The photograph was taken at an angle. The head or neck is involved. Reported duration is less than one week — 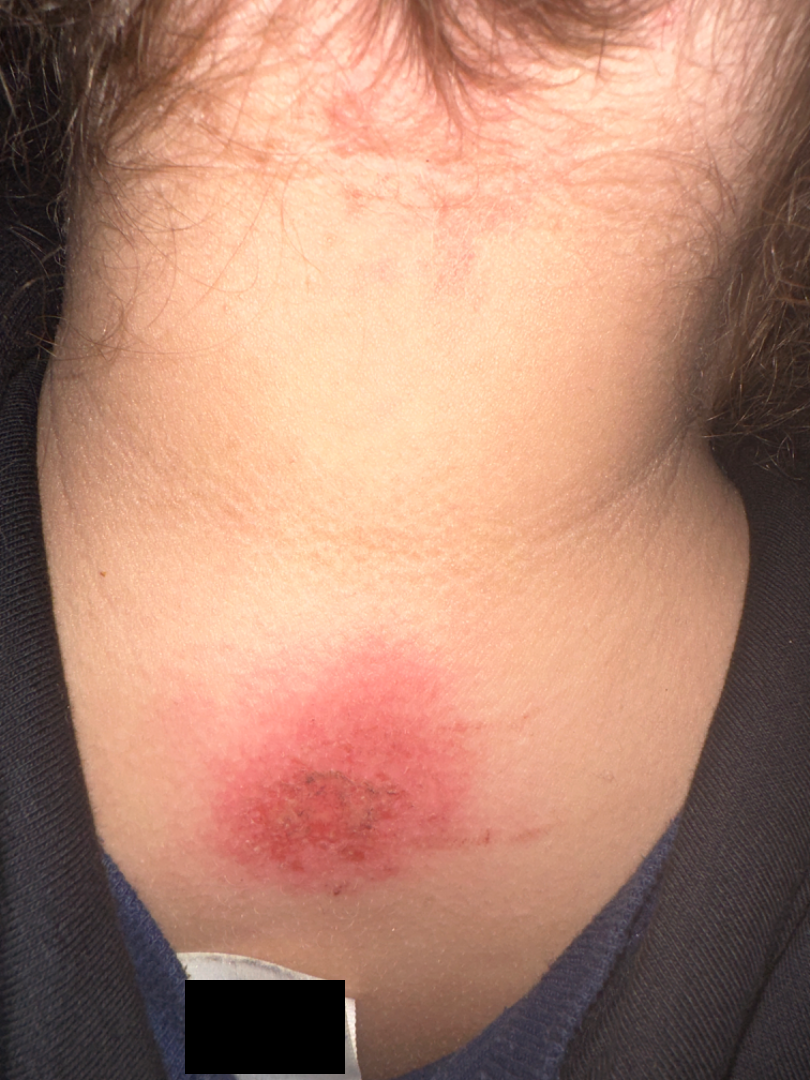Q: What conditions are considered?
A: Eczema (0.67); Irritant Contact Dermatitis (0.33)